Present for one to four weeks. The subject is 40–49, male. The lesion is described as raised or bumpy. The back of the hand and arm are involved. The patient considered this a rash. Reported lesion symptoms include itching. A close-up photograph: 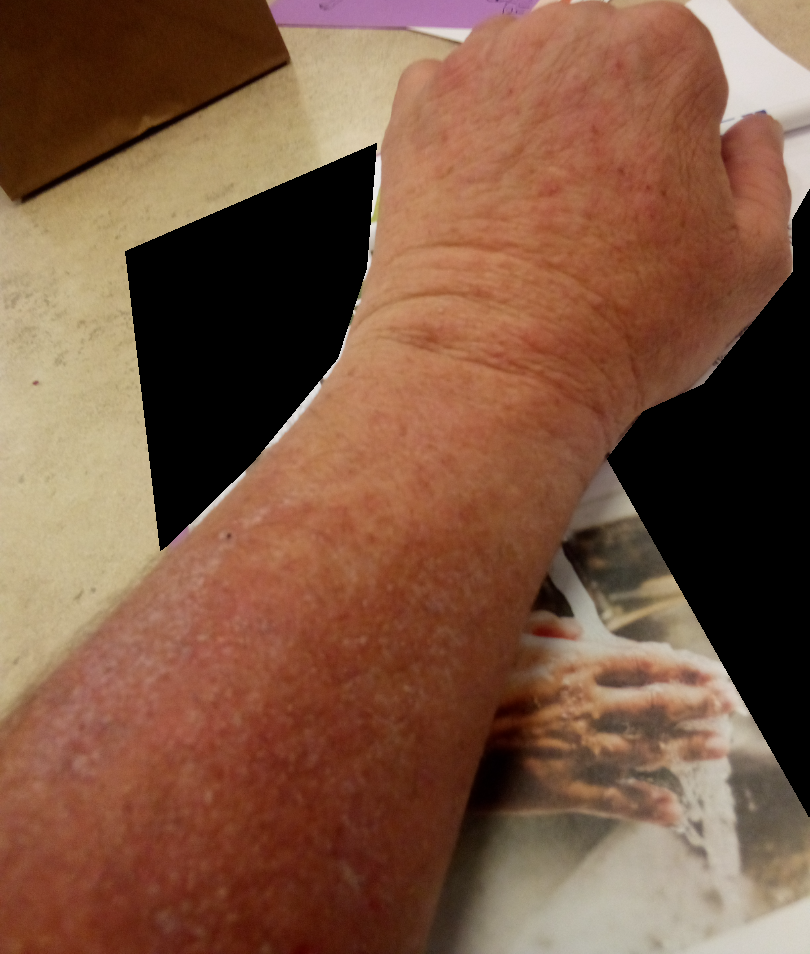{"differential": {"Eczema": 0.67, "Psoriasis": 0.33}}